Female contributor, age 60–69. The photo was captured at a distance. The affected area is the leg: 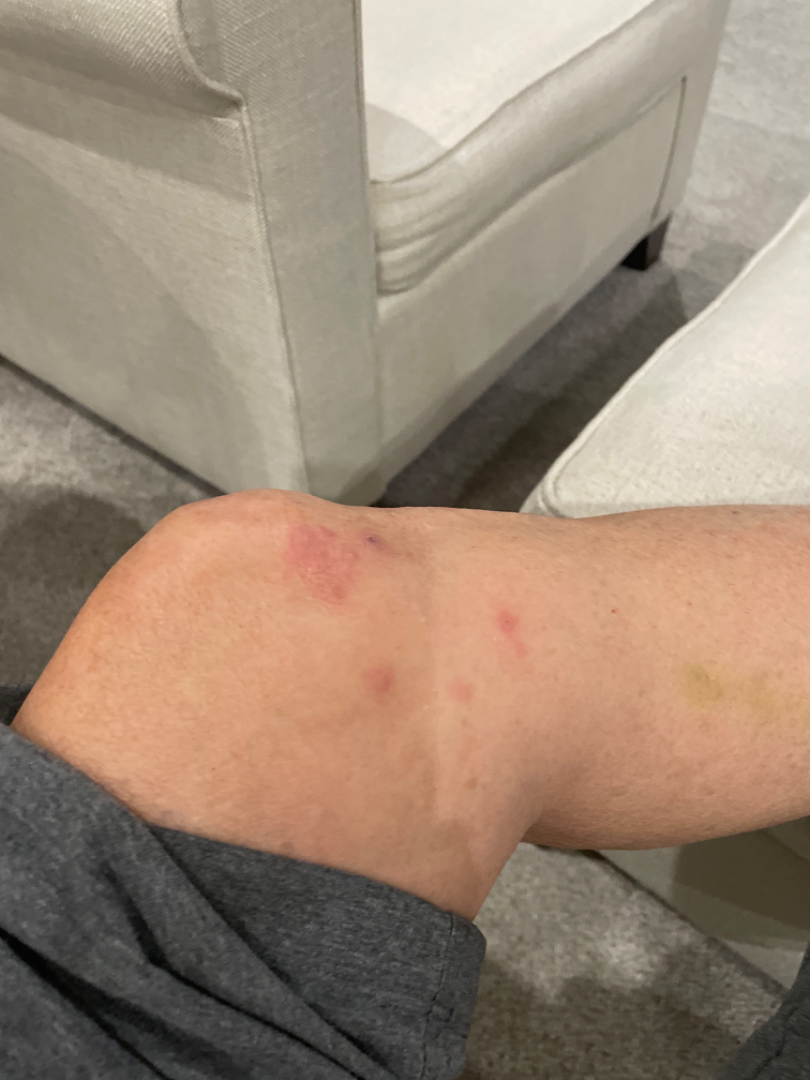Self-categorized by the patient as a rash.
The lesion is described as raised or bumpy.
Associated systemic symptoms include joint pain.
On photographic review by a dermatologist, the impression was split between Skin infection and Folliculitis; less probable is Eczema.